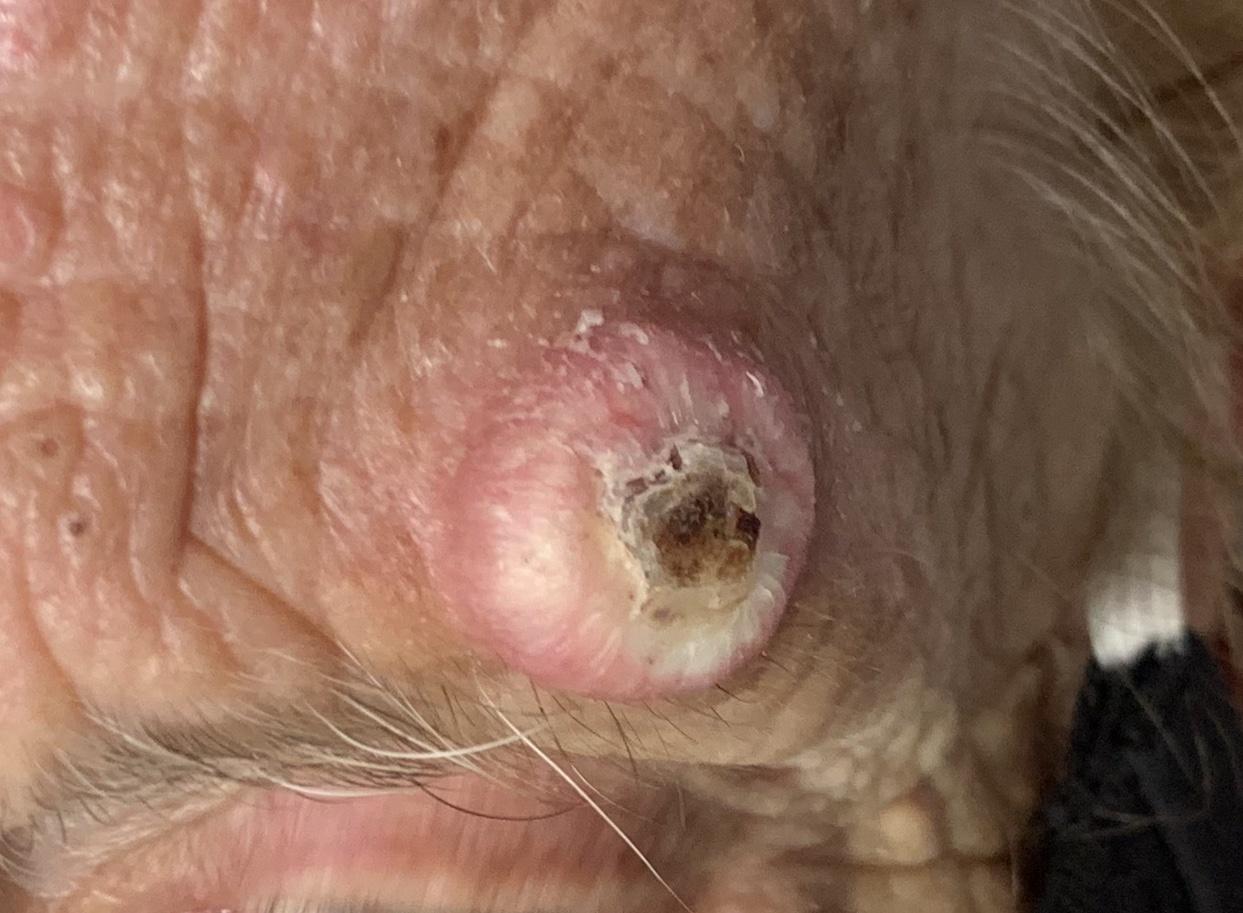| field | value |
|---|---|
| imaging | clinical overview photograph |
| skin type | II |
| patient | female, roughly 85 years of age or older |
| anatomic site | the head or neck |
| diagnosis | Squamous cell carcinoma (biopsy-proven) |